The affected area is the leg; this is a close-up image.
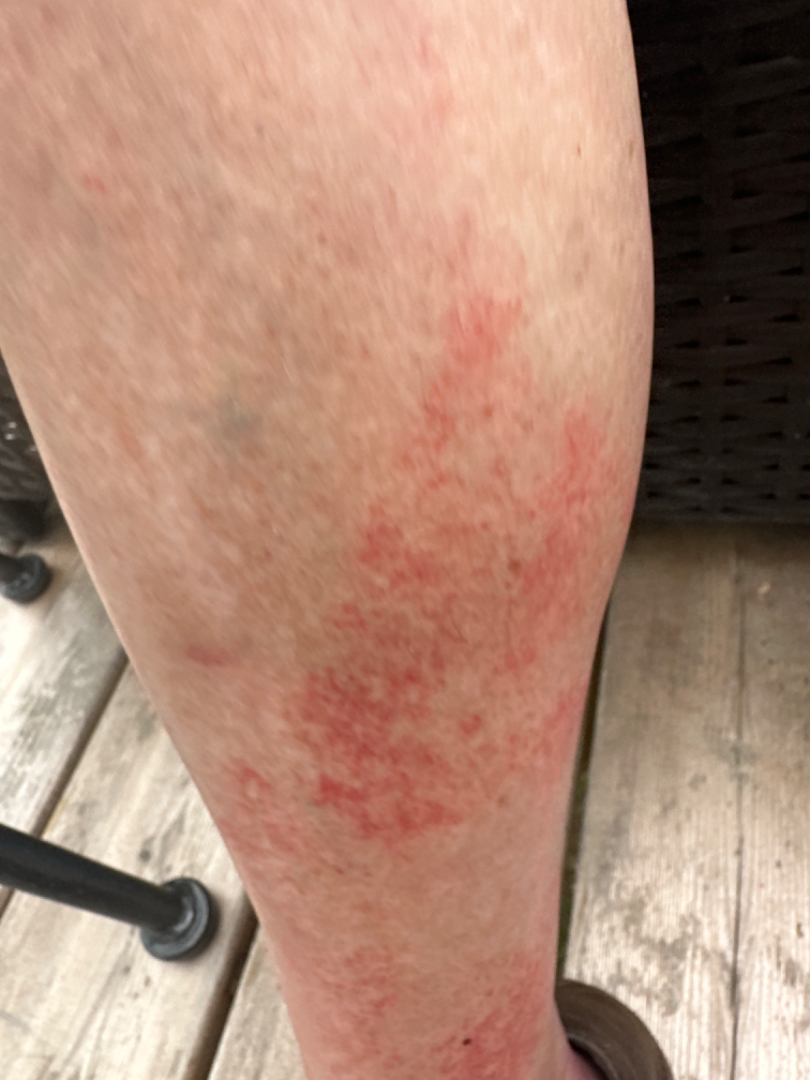The lesion is described as flat. The condition has been present for less than one week. The patient reported no relevant symptoms from the lesion. Fitzpatrick I; lay reviewers estimated MST 2. Pigmented purpuric eruption (55%); Leukocytoclastic Vasculitis (27%); Allergic Contact Dermatitis (18%).